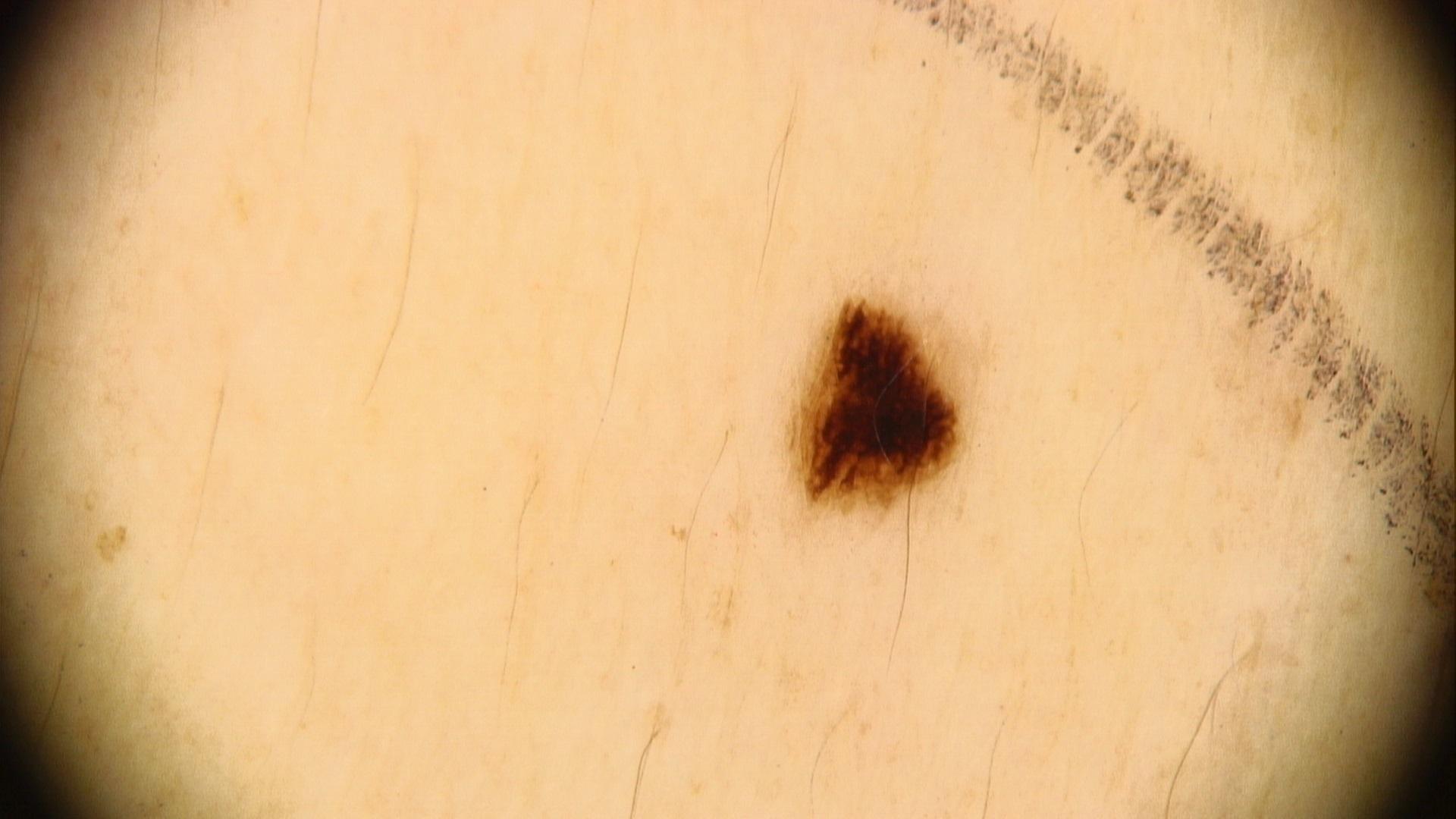image type=contact-polarized dermoscopy | melanoma history=melanoma in a first-degree relative but no previous melanoma | anatomic site=a lower extremity | assessment=Nevus.